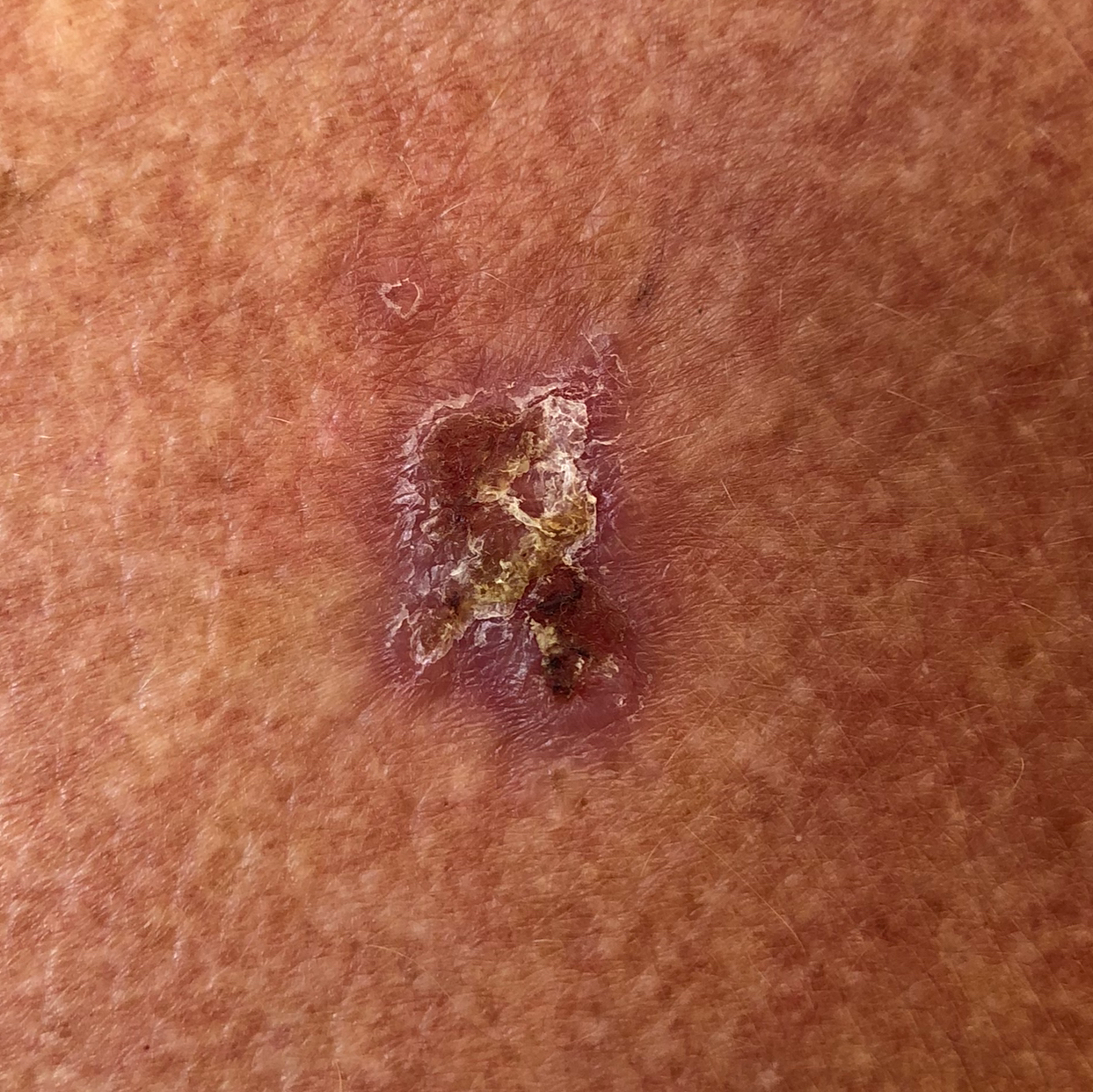Patient and lesion:
A clinical photograph showing a skin lesion. A male subject in their early 60s.
Conclusion:
Biopsy-confirmed as a basal cell carcinoma.